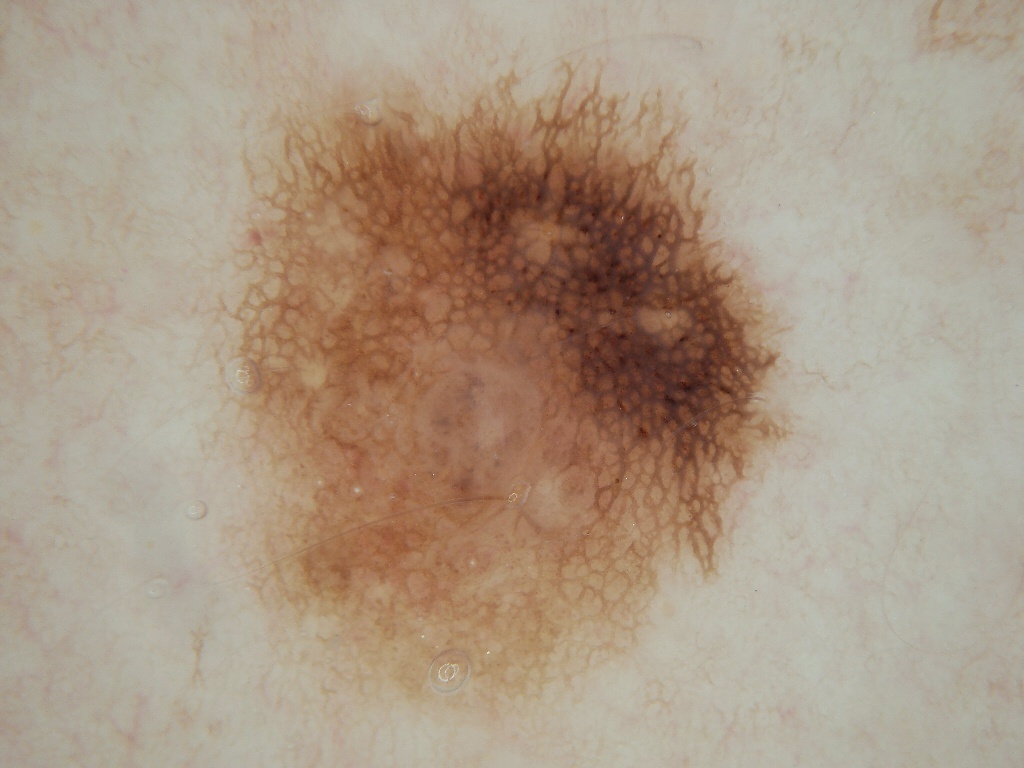Q: How was this image acquired?
A: dermoscopic image
Q: Where is the lesion in the image?
A: [228,60,790,721]
Q: What dermoscopic features are not present?
A: streaks and globules
Q: How large is the lesion within the image?
A: ~35% of the field
Q: What did the assessment conclude?
A: a benign skin lesion